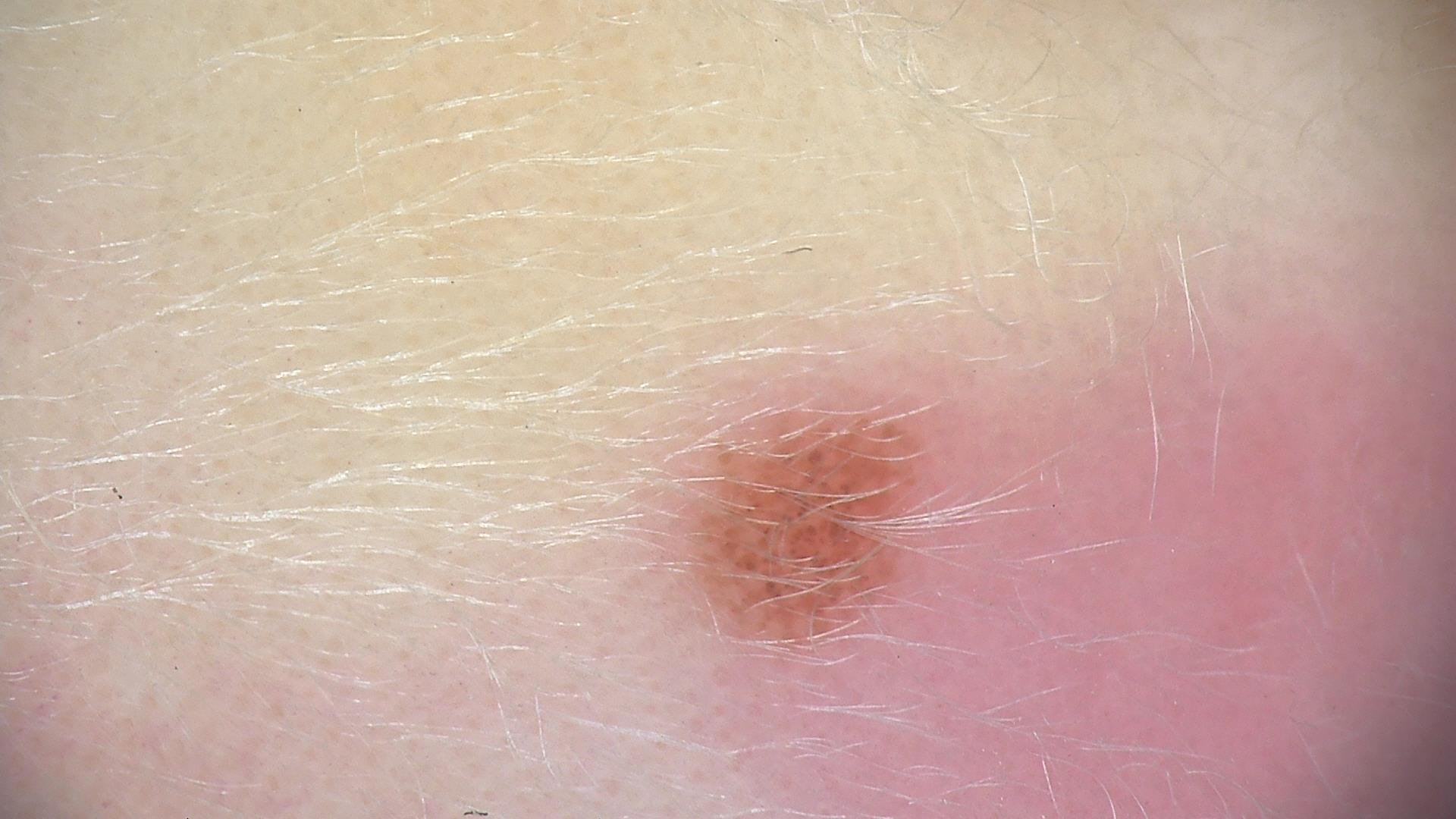Findings:
A dermoscopic close-up of a skin lesion.
Impression:
Classified as a banal lesion — a compound nevus.